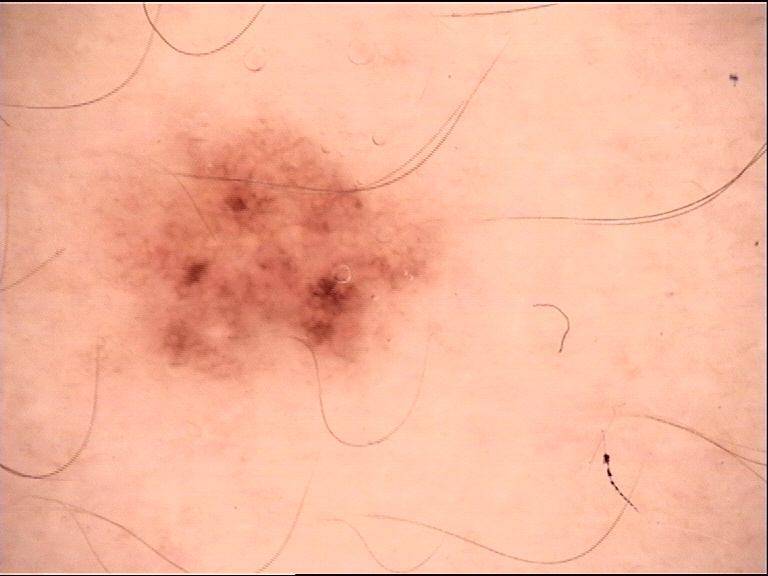Findings:
A dermatoscopic image of a skin lesion.
Impression:
Labeled as a dysplastic junctional nevus.